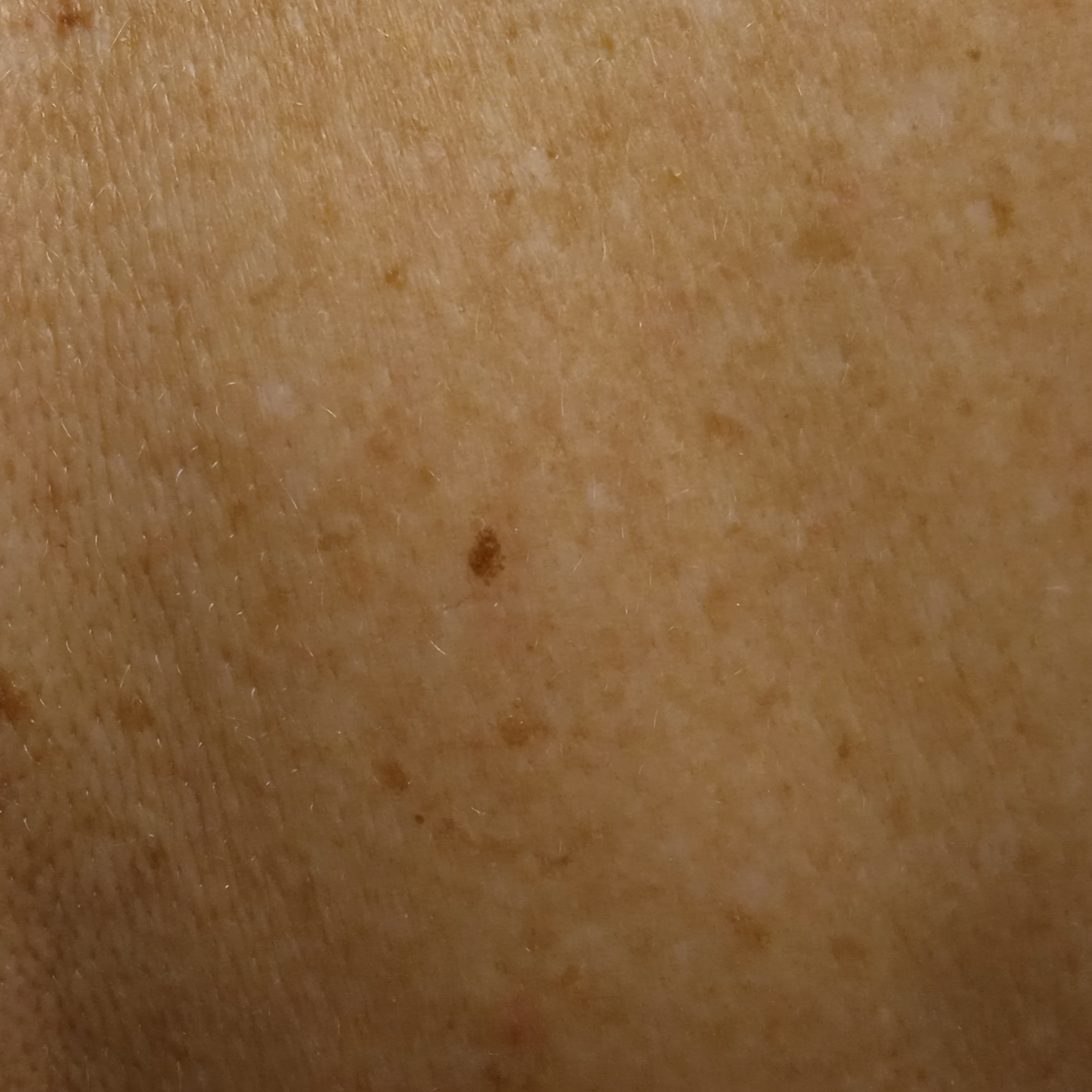The patient says their skin reddens with sun exposure.
A female patient 73 years old.
A clinical photograph of a skin lesion.
Imaged for a research study, with no referral diagnosis recorded.
On a questionnaire the patient reported no prior organ transplant and no sunbed use.
The patient describes having few moles overall.
Located on the back.
The lesion is about 3.9 mm across.
Dermatologist review favored a seborrheic keratosis.